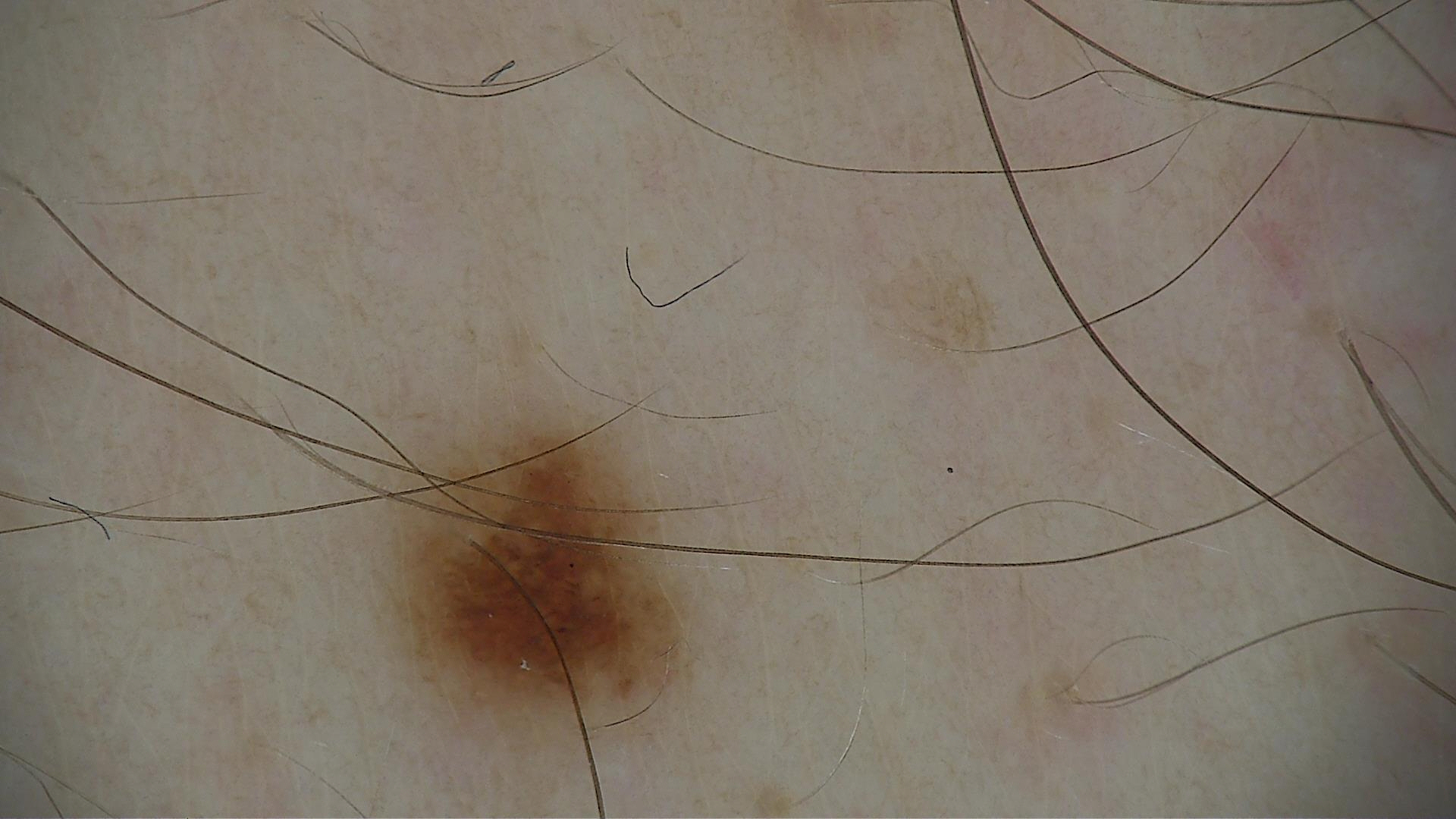{"image": "dermoscopy", "diagnosis": {"name": "junctional nevus", "code": "jb", "malignancy": "benign", "super_class": "melanocytic", "confirmation": "expert consensus"}}